This image was taken at a distance: 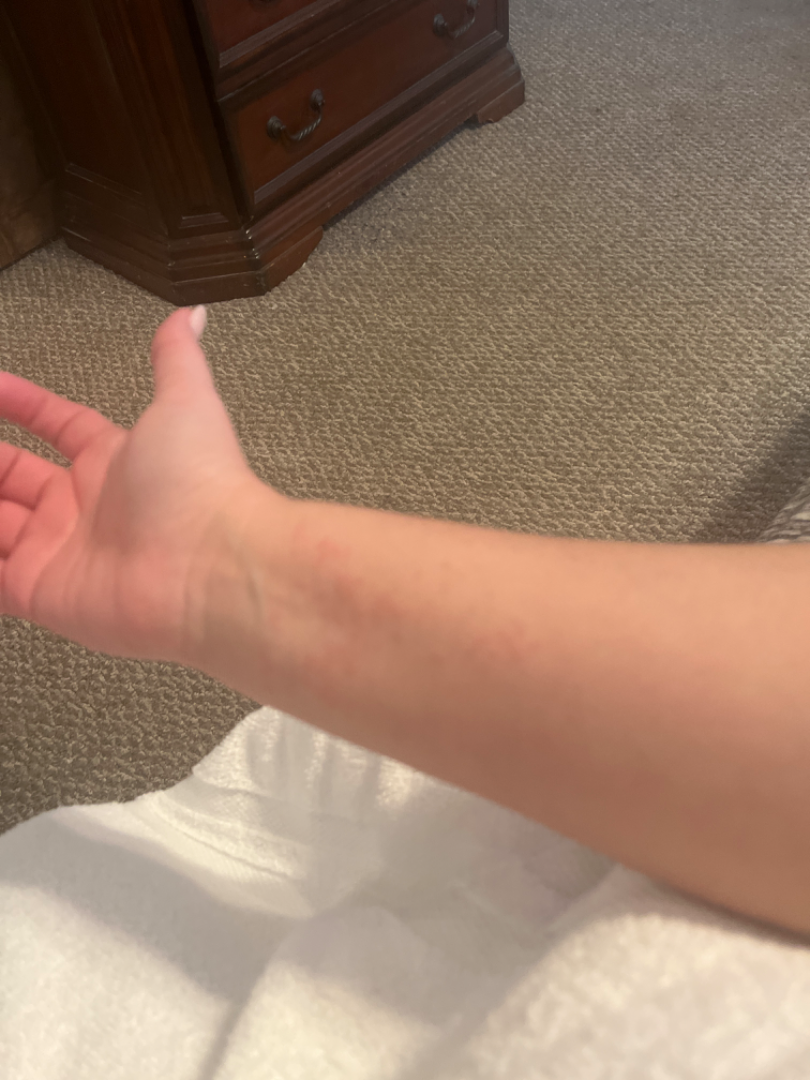assessment = not assessable.